The photograph is a close-up of the affected area · the patient is a female aged 18–29 · the lesion involves the front of the torso:
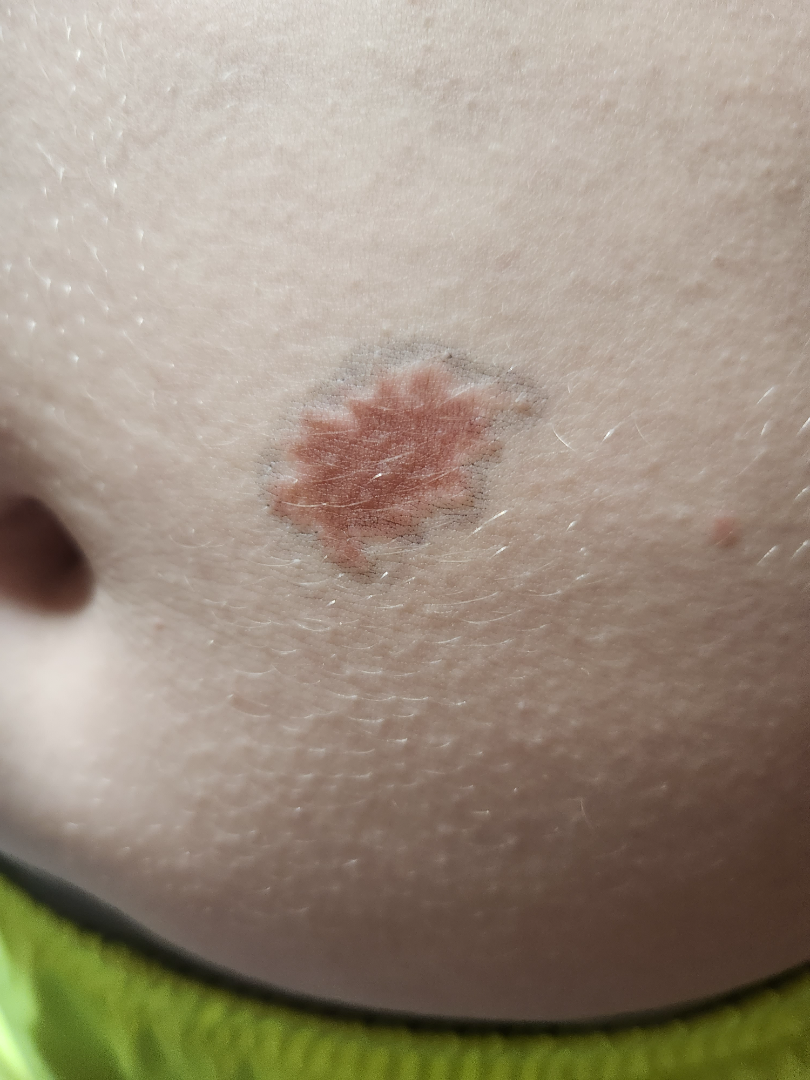Review:
On independent review by the dermatologists: the favored diagnosis is Melanocytic Nevus; also consider Atypical Nevus; also on the differential is Melanoma.